Located on the leg; this image was taken at an angle; the contributor is 40–49, female.
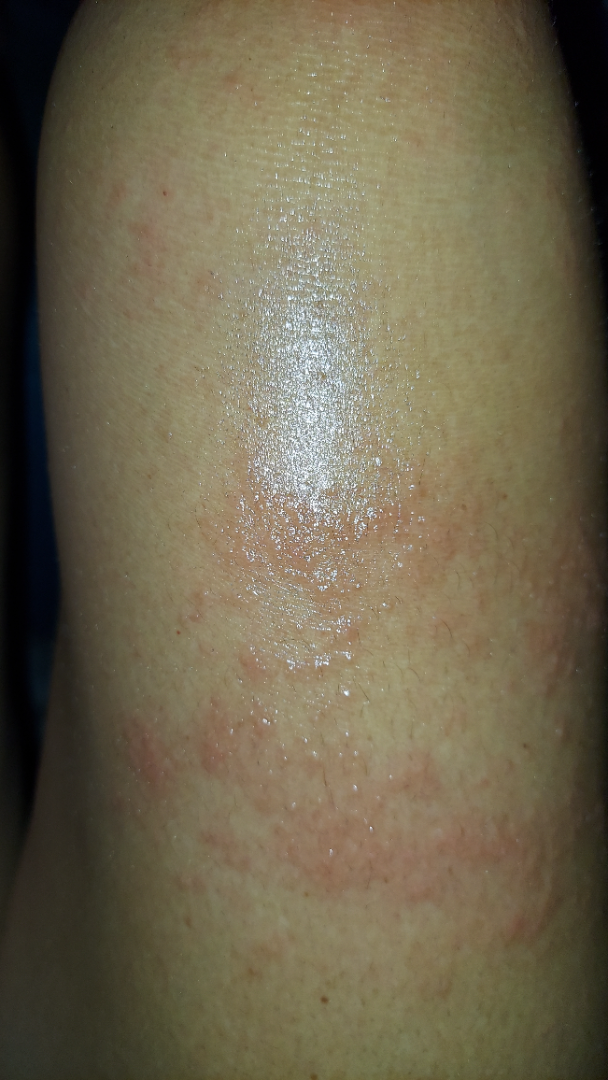Q: What is the differential diagnosis?
A: the favored diagnosis is Allergic Contact Dermatitis